Skin tone: Fitzpatrick skin type IV. This is a close-up image: 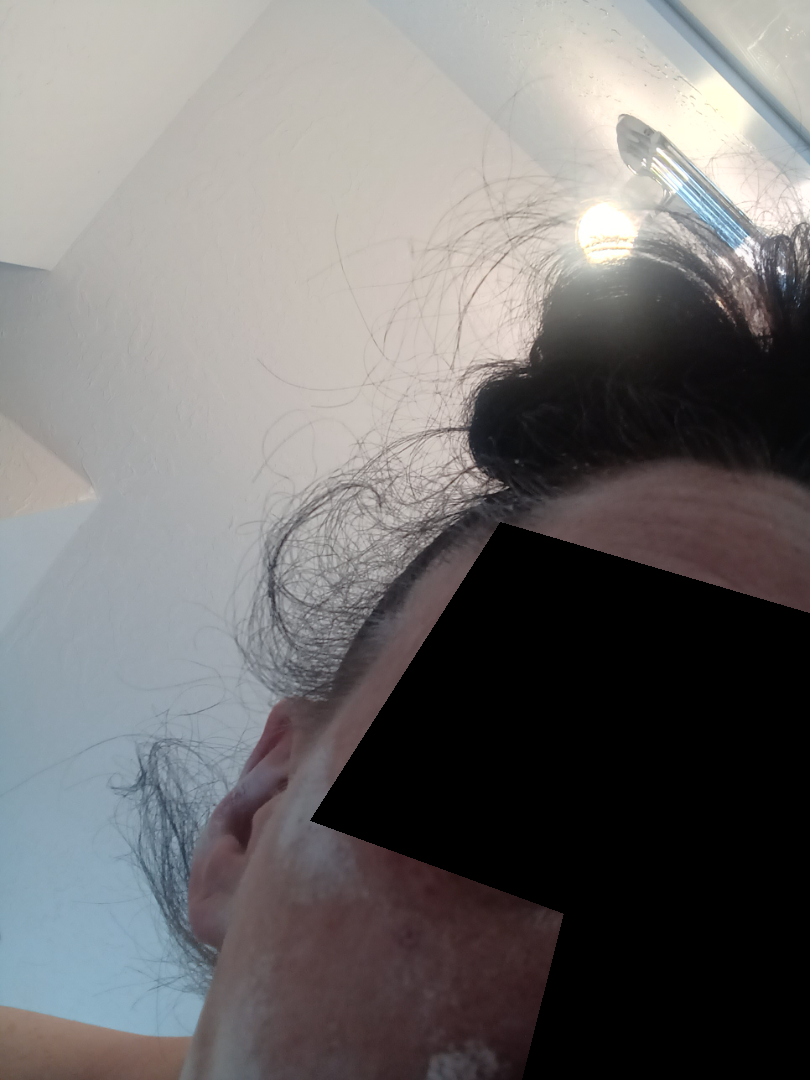Impression: The condition could not be reliably identified from the image.